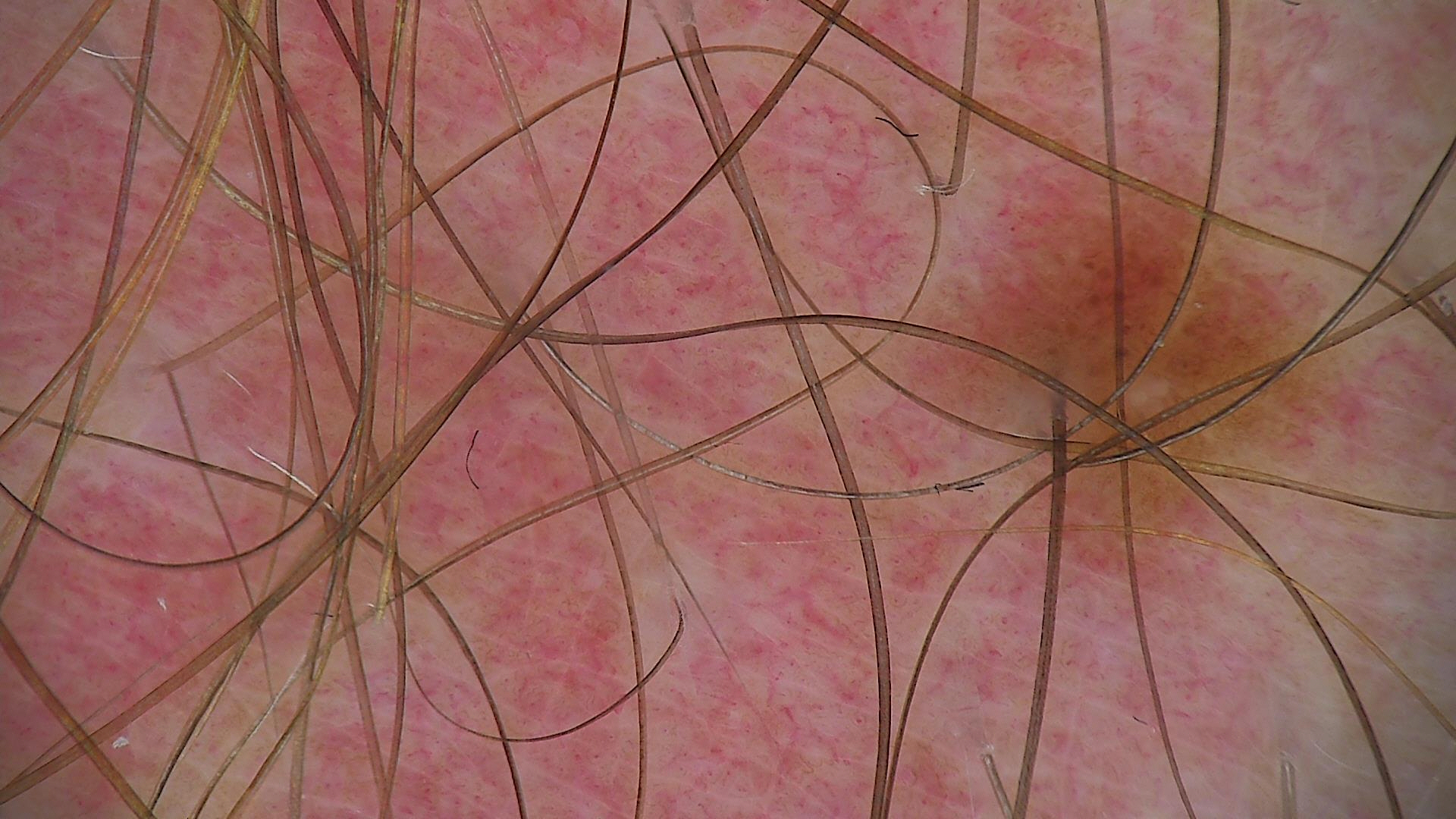modality = dermoscopy; class = junctional nevus (expert consensus).